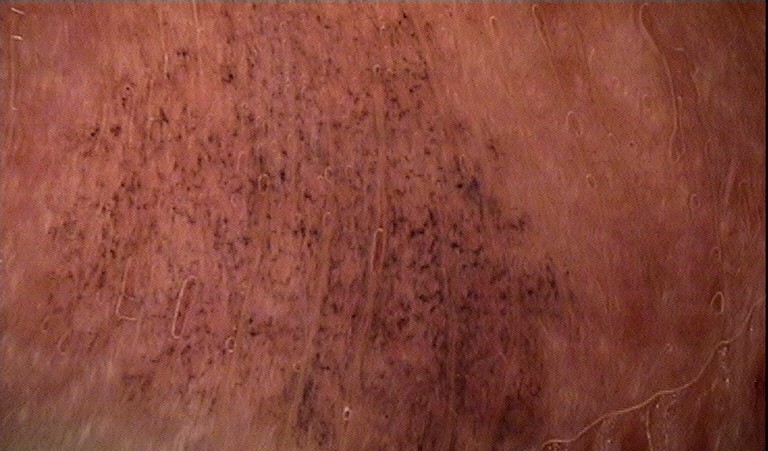A dermoscopic image of a skin lesion. The diagnostic label was a benign lesion — an ink-spot lentigo.